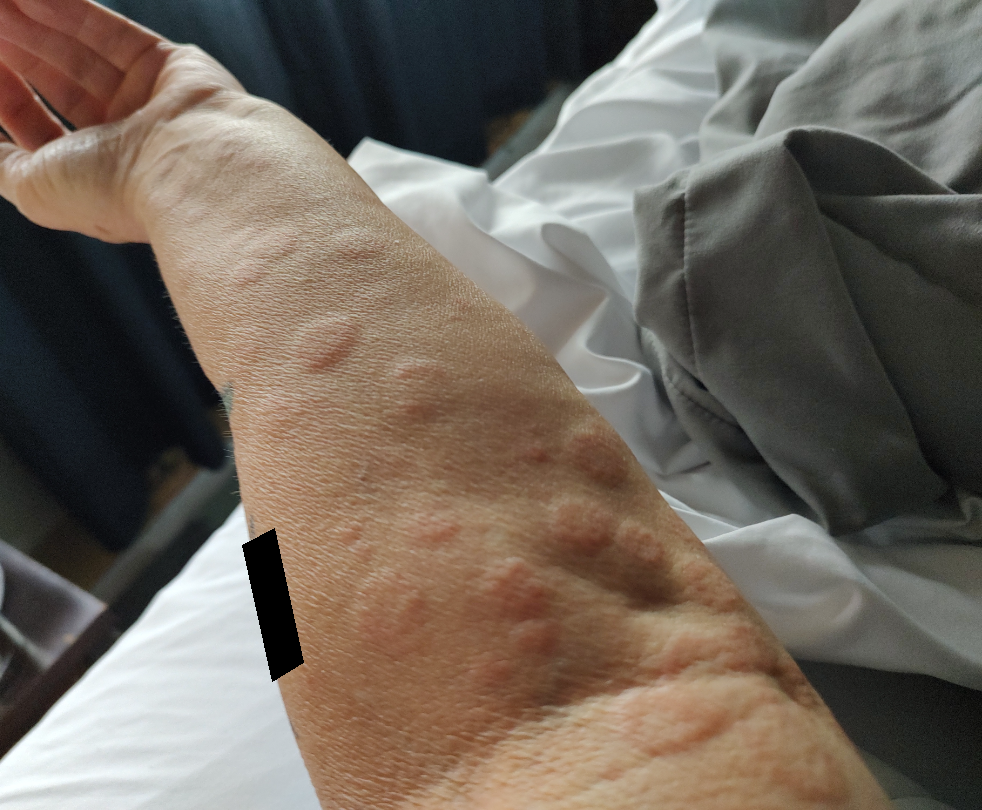diagnostic considerations = Cutaneous metastasis (0.54); Urticaria (0.23); Pseudolymphoma (0.23).